A dermoscopic image of a skin lesion:
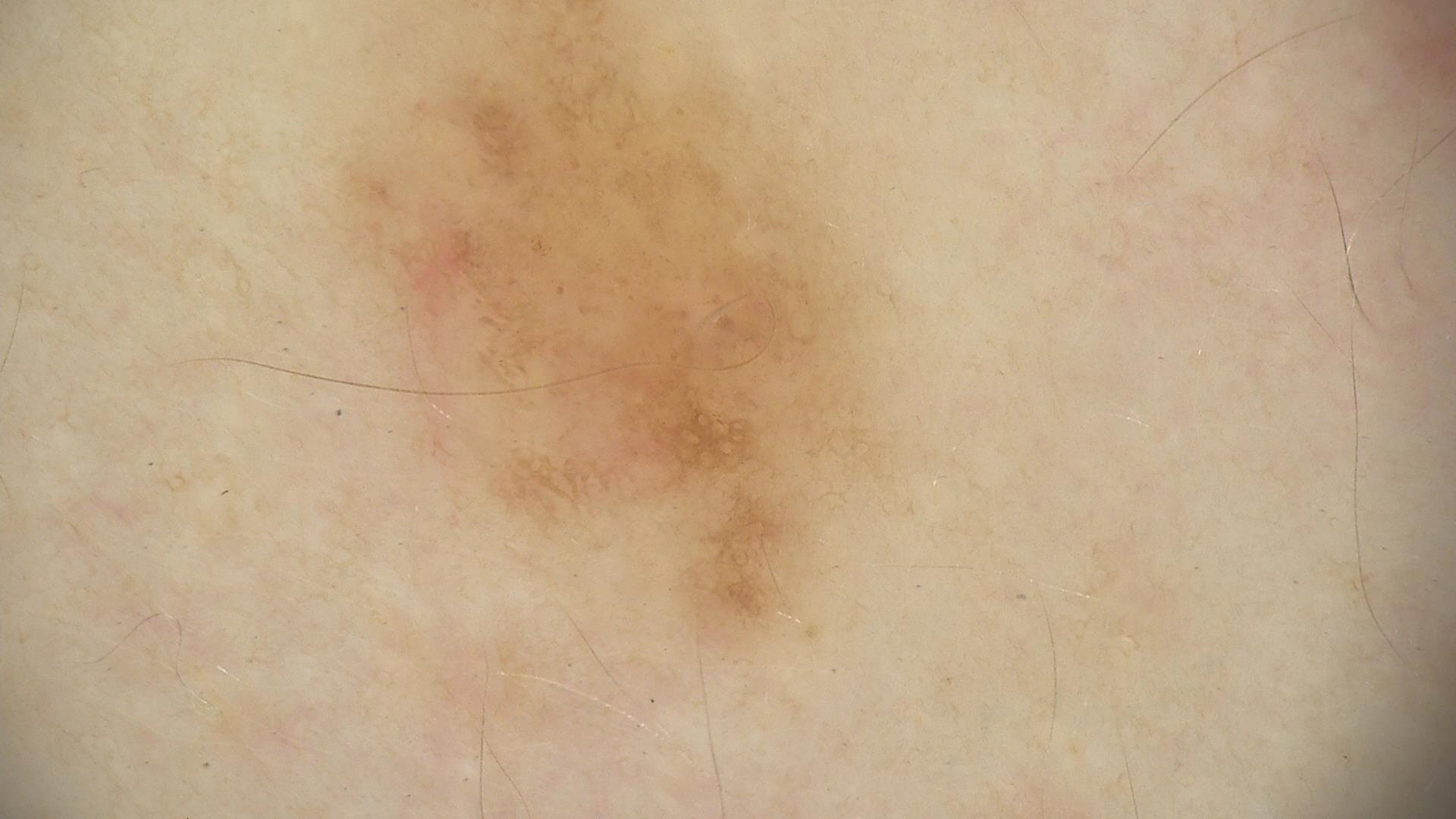Impression:
Classified as a dysplastic junctional nevus.